Close-up view: 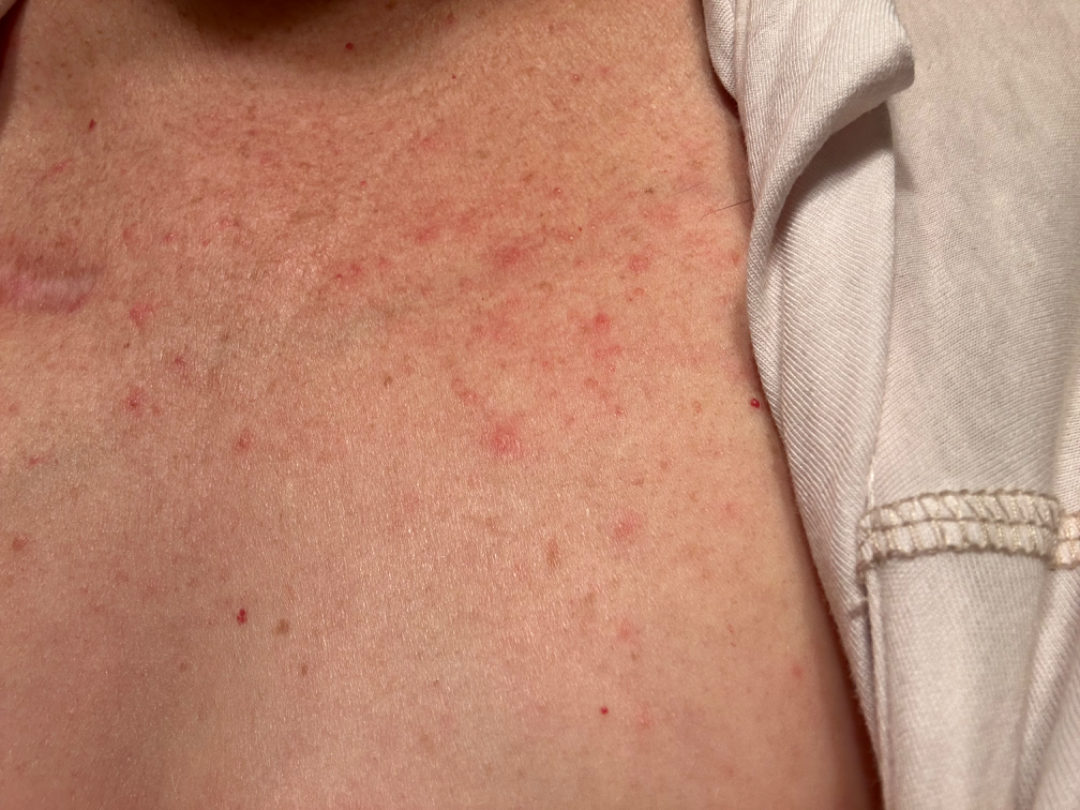Assessment: The impression was split between Acne and Folliculitis; less probable is Grover's disease.